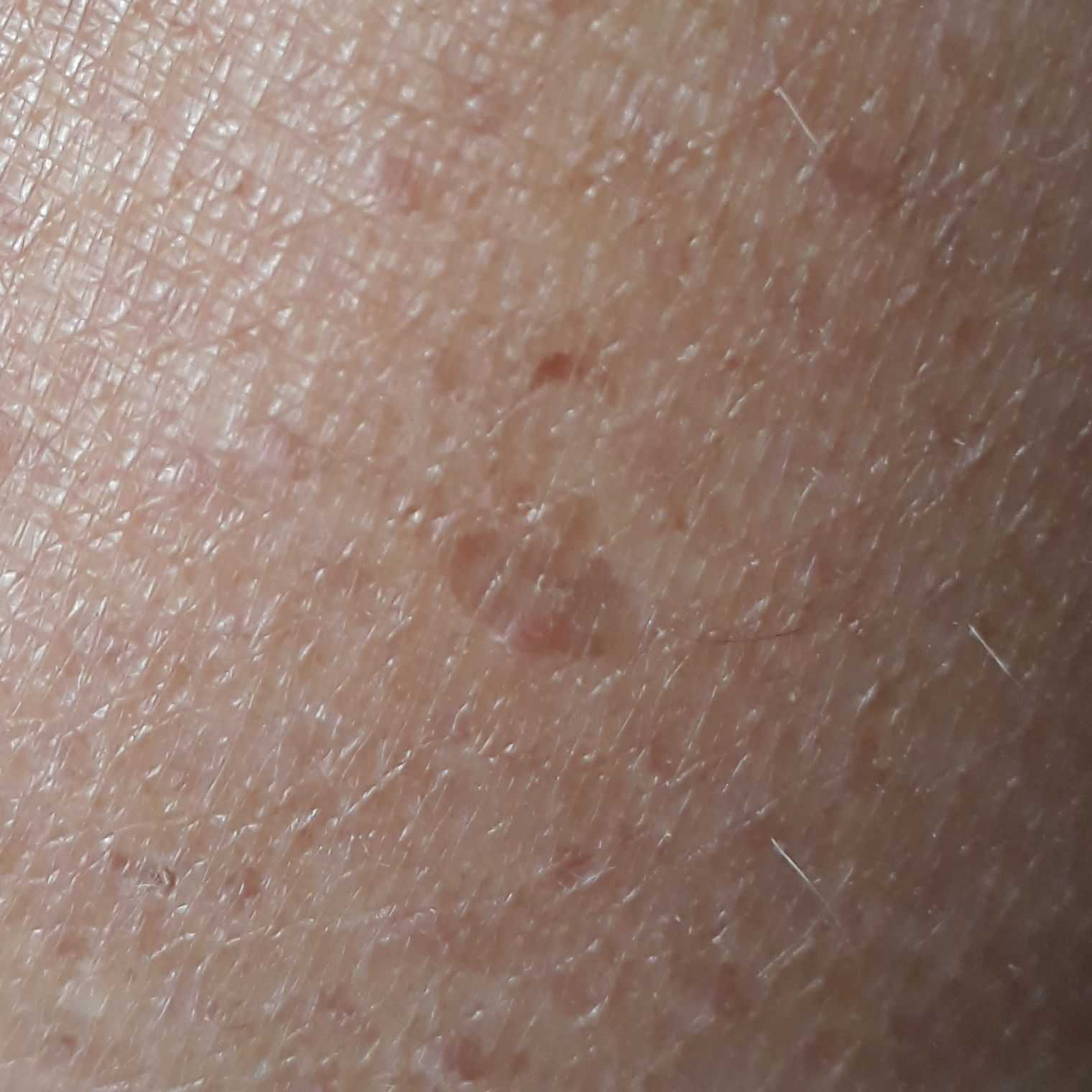A clinical close-up photograph of a skin lesion. The lesion is located on a thigh. The patient describes that the lesion is elevated and has grown, but does not itch. Consistent with a benign lesion — a seborrheic keratosis.